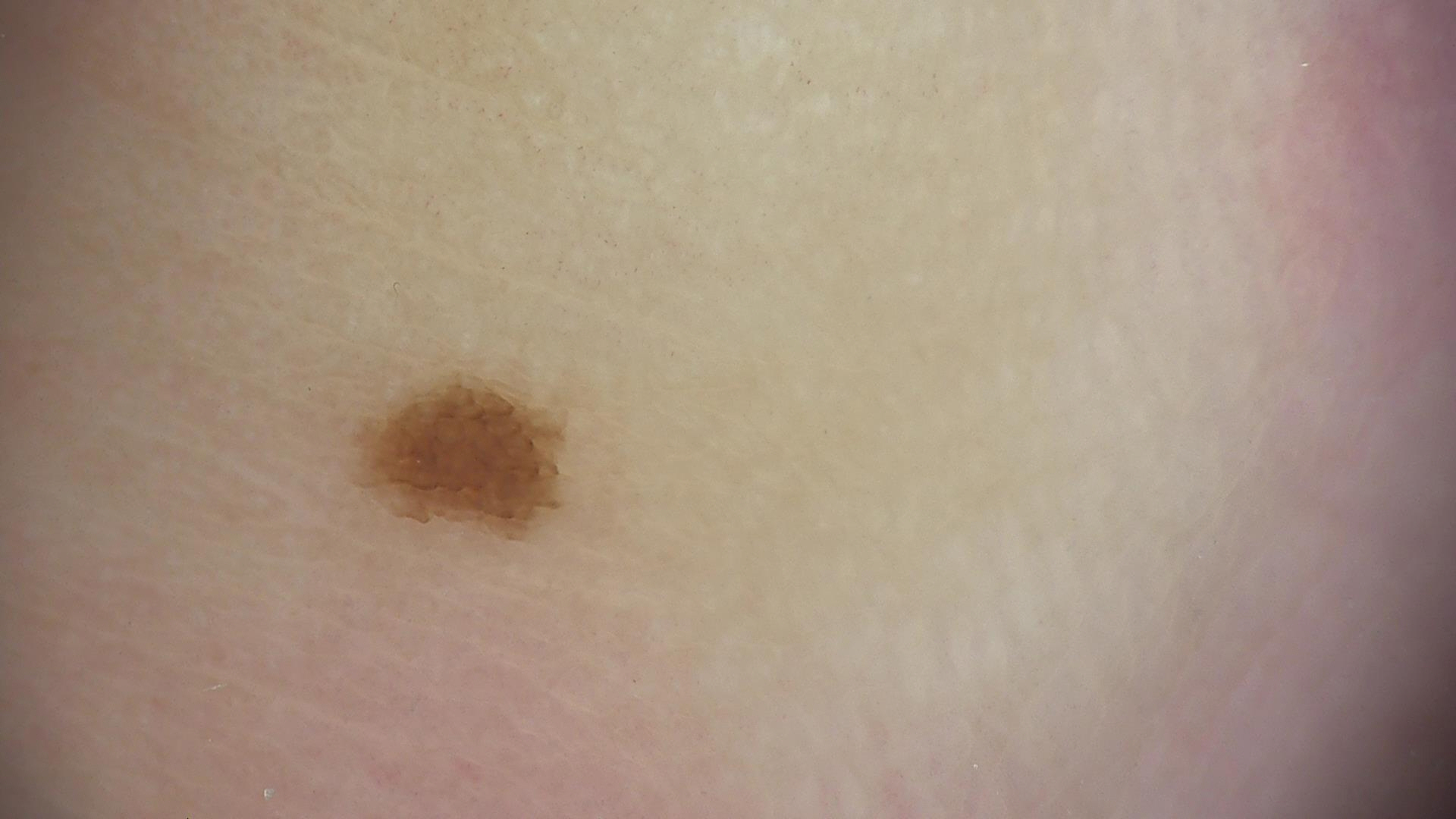A dermoscopy image of a single skin lesion. The diagnostic label was a banal lesion — an acral junctional nevus.